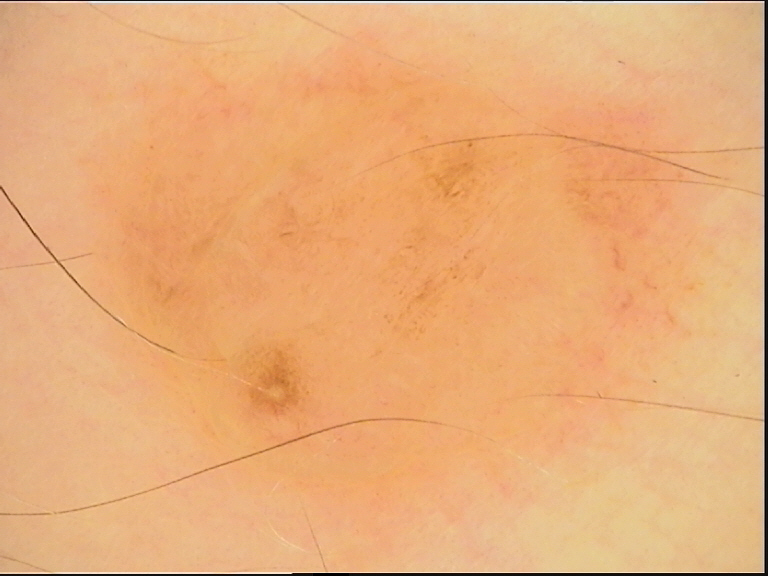  lesion_type:
    main_class: banal
    pattern: dermal
  diagnosis:
    name: dermal nevus
    code: db
    malignancy: benign
    super_class: melanocytic
    confirmation: expert consensus